A skin lesion imaged with a dermatoscope: 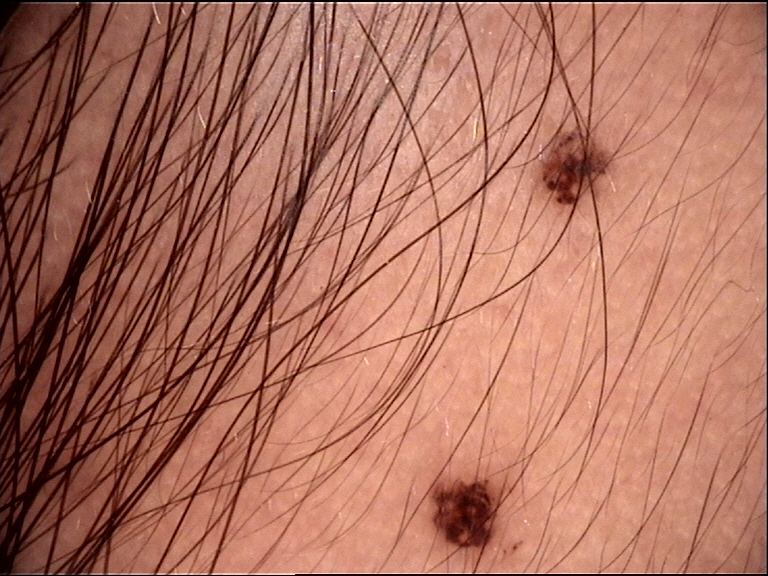diagnostic label = dysplastic junctional nevus (expert consensus).